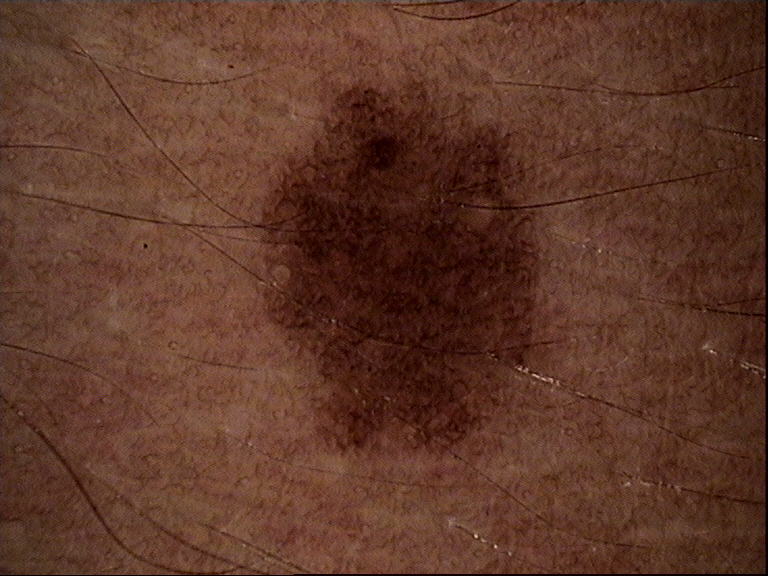Findings:
- assessment — dysplastic junctional nevus (expert consensus)